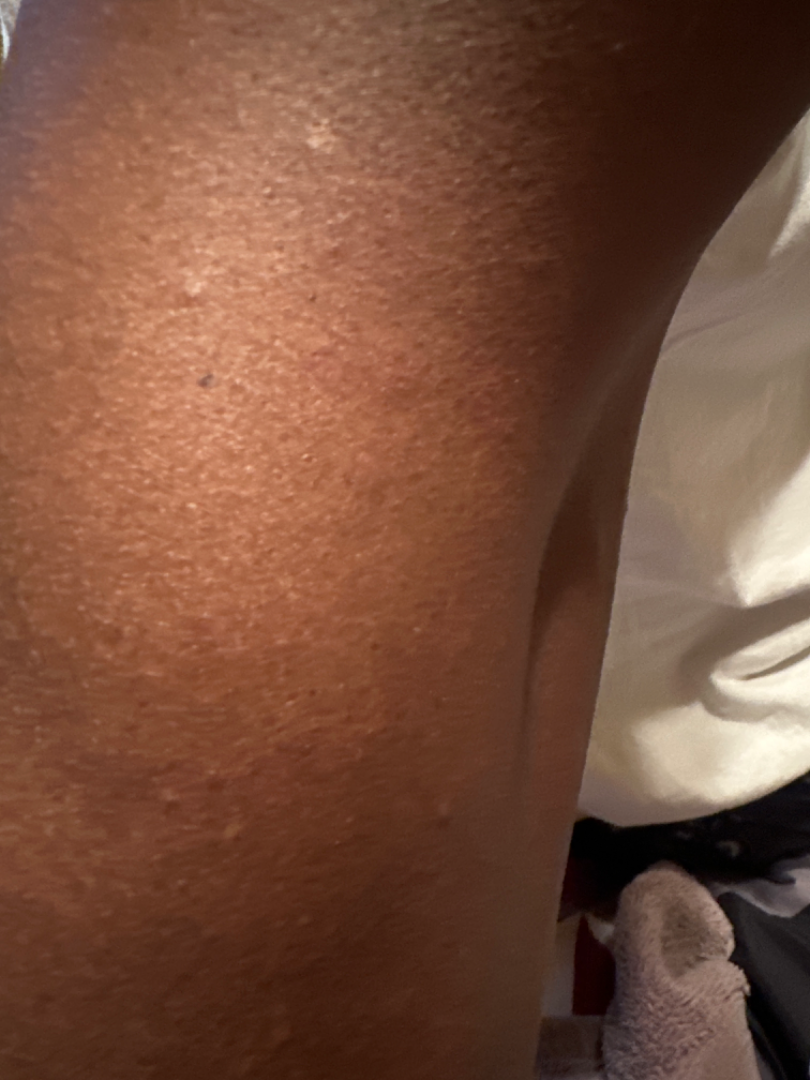Q: Could the case be diagnosed?
A: could not be assessed
Q: What is the lesion texture?
A: raised or bumpy
Q: Anatomic location?
A: front of the torso, leg and arm
Q: Duration?
A: less than one week
Q: Image view?
A: close-up
Q: Reported symptoms?
A: itching
Q: Patient's own categorization?
A: a rash